A female patient age 39. Collected as part of a research study, without a referral diagnosis. Dermoscopy of a skin lesion:
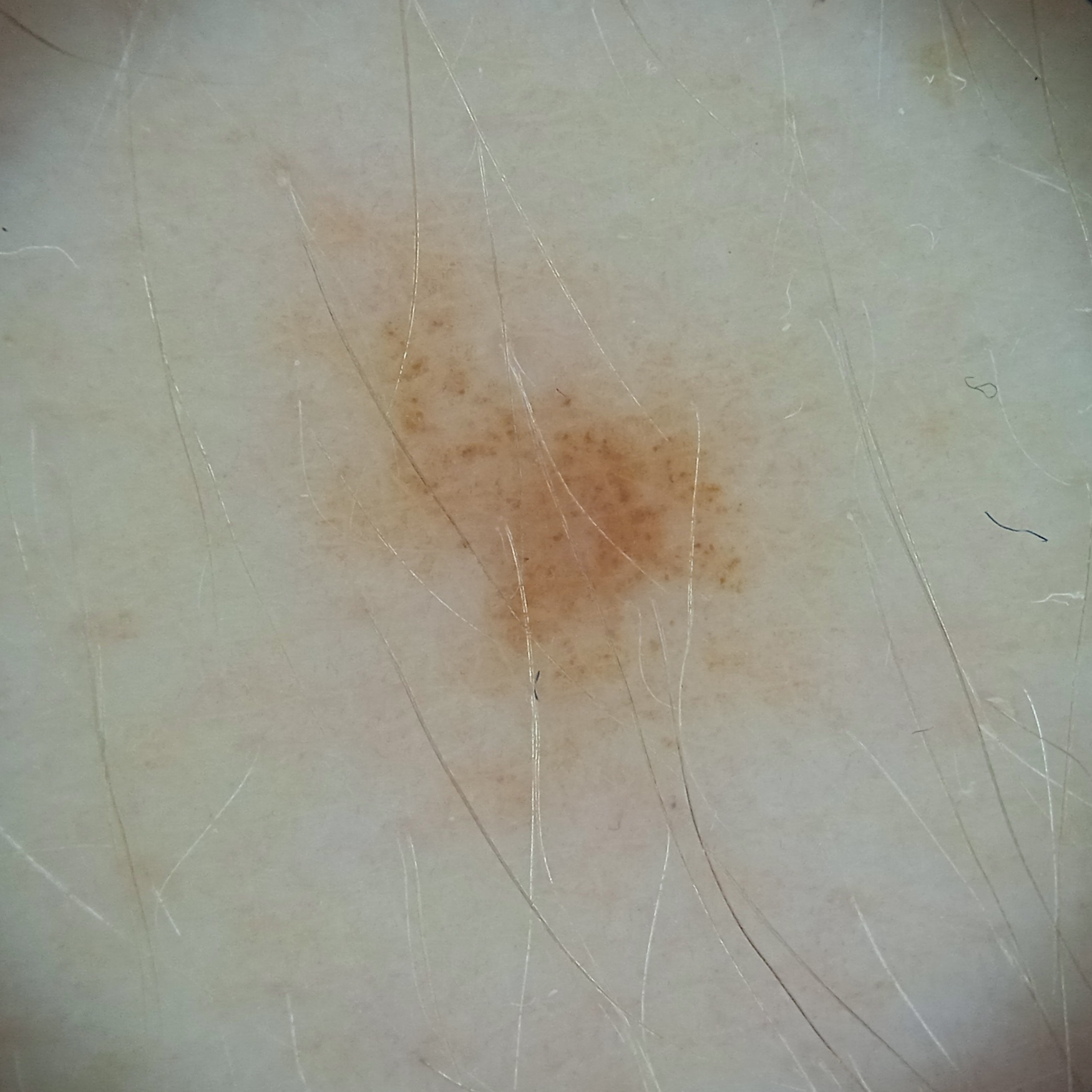lesion_location: an arm
lesion_size:
  diameter_mm: 5.1
diagnosis:
  name: melanocytic nevus
  malignancy: benign